A dermoscopic photograph of a skin lesion:
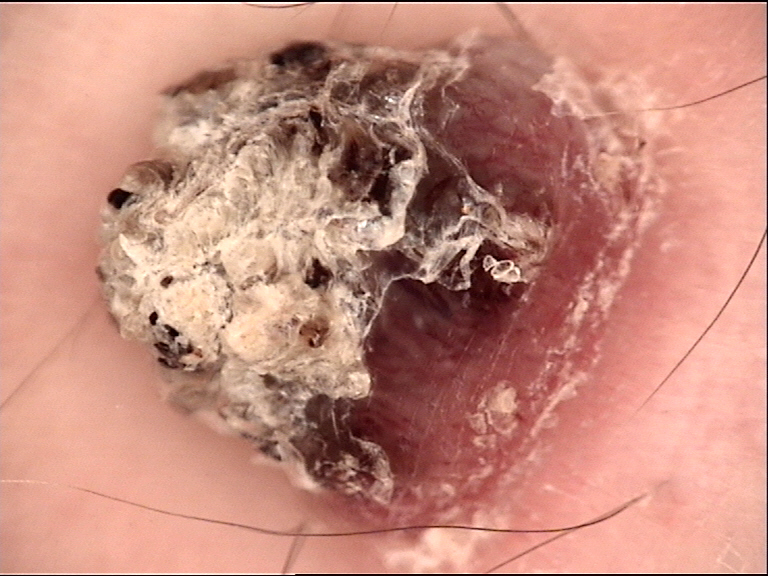Q: What kind of lesion is this?
A: keratinocytic
Q: What is this lesion?
A: cutaneous horn (biopsy-proven)